A male subject aged 13-17, a dermoscopic close-up of a skin lesion:
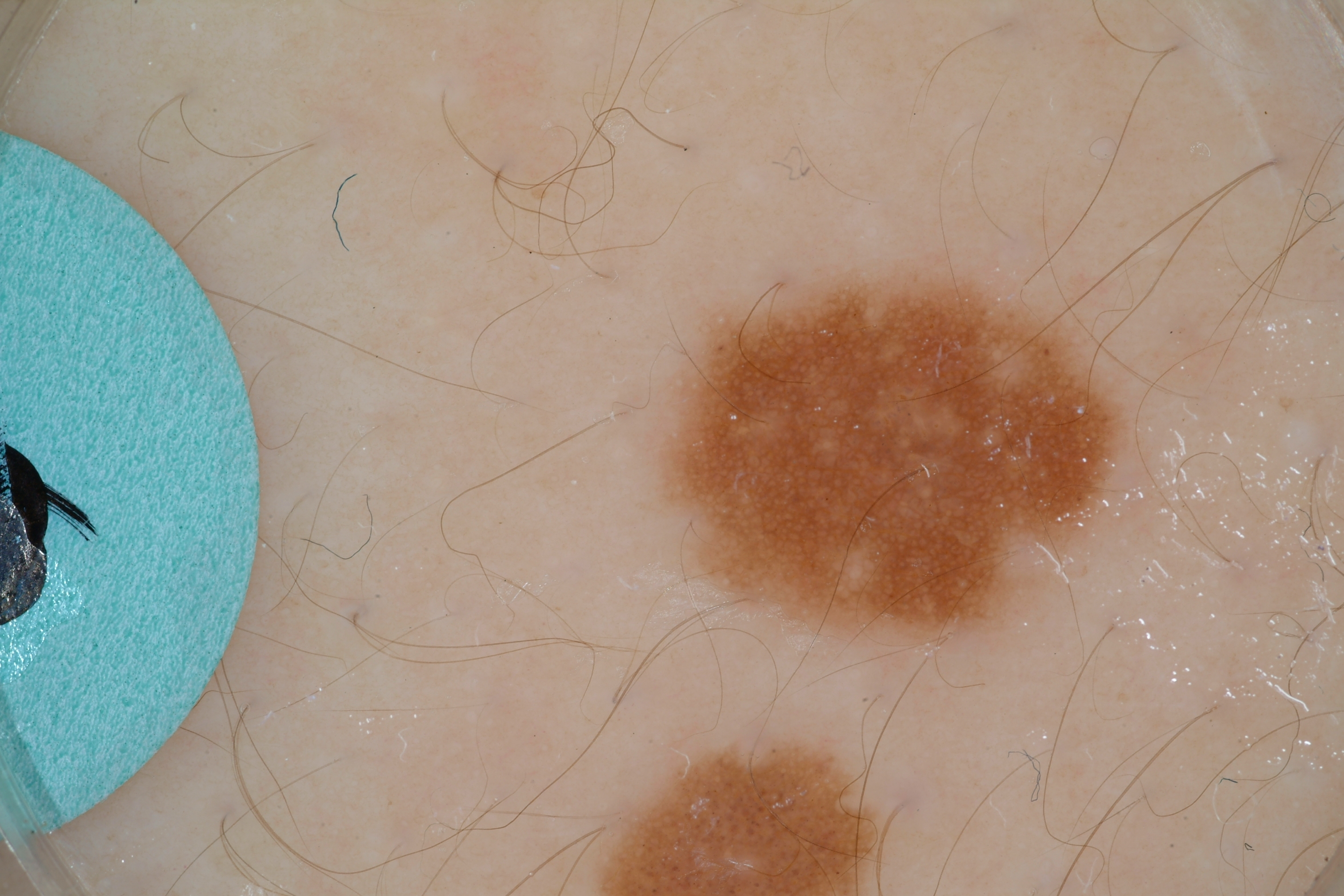Case summary:
- location — [612, 229, 1174, 681]
- features — pigment network; absent: milia-like cysts, negative network, and streaks
- impression — a melanocytic nevus, a benign skin lesion